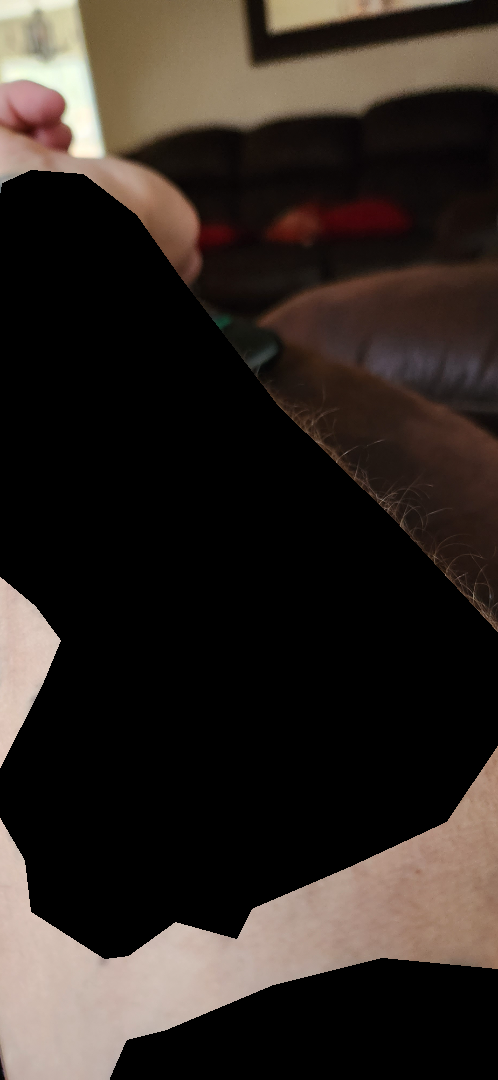Assessment:
The skin findings could not be characterized from the image.